Located on the top or side of the foot and arm · an image taken at a distance · the subject is male: 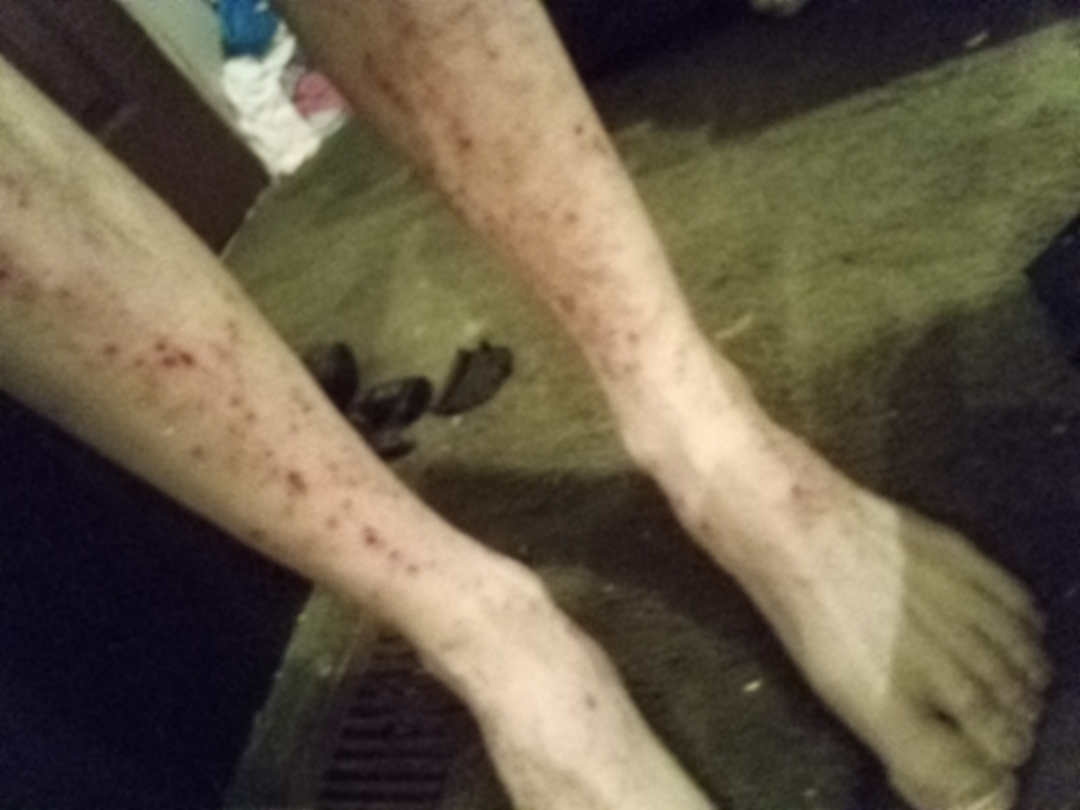Impression: On dermatologist assessment of the image, Insect Bite and Eczema were each considered, in no particular order.